Symptoms reported: itching and burning. Reported duration is one to three months. The photo was captured at a distance. The patient notes the lesion is rough or flaky. The lesion involves the arm. The subject is female. The patient described the issue as a rash.
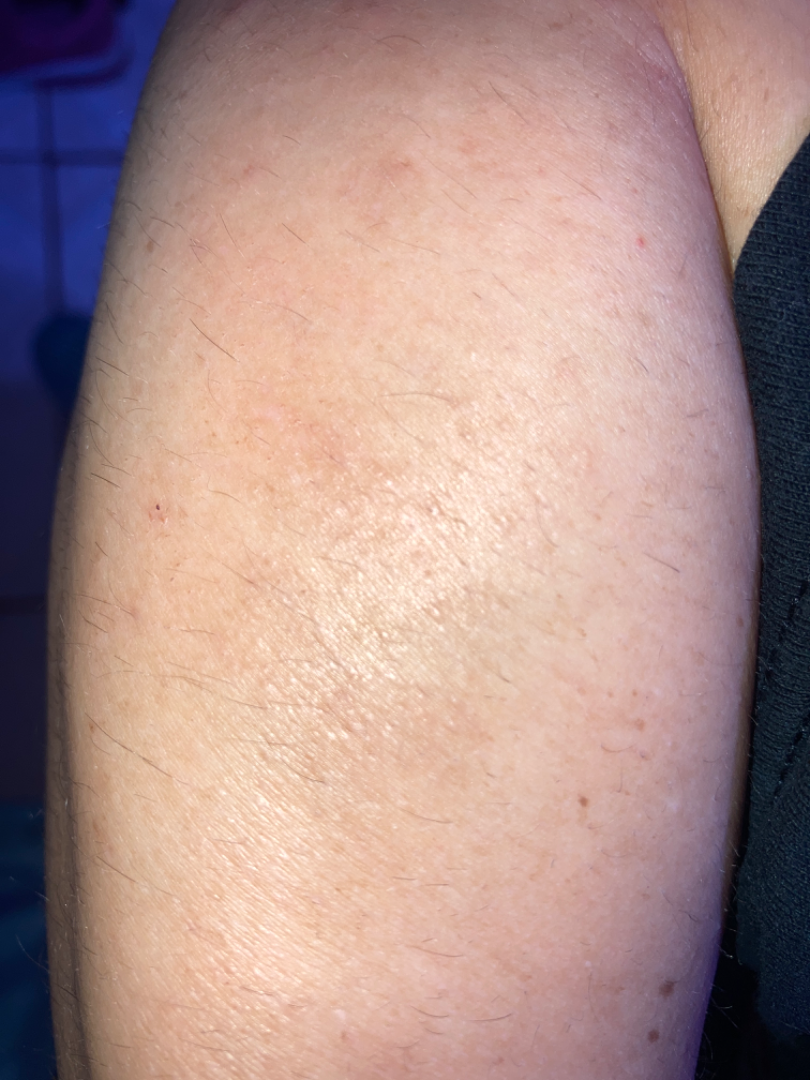Reviewed remotely by three dermatologists: most consistent with Eczema.